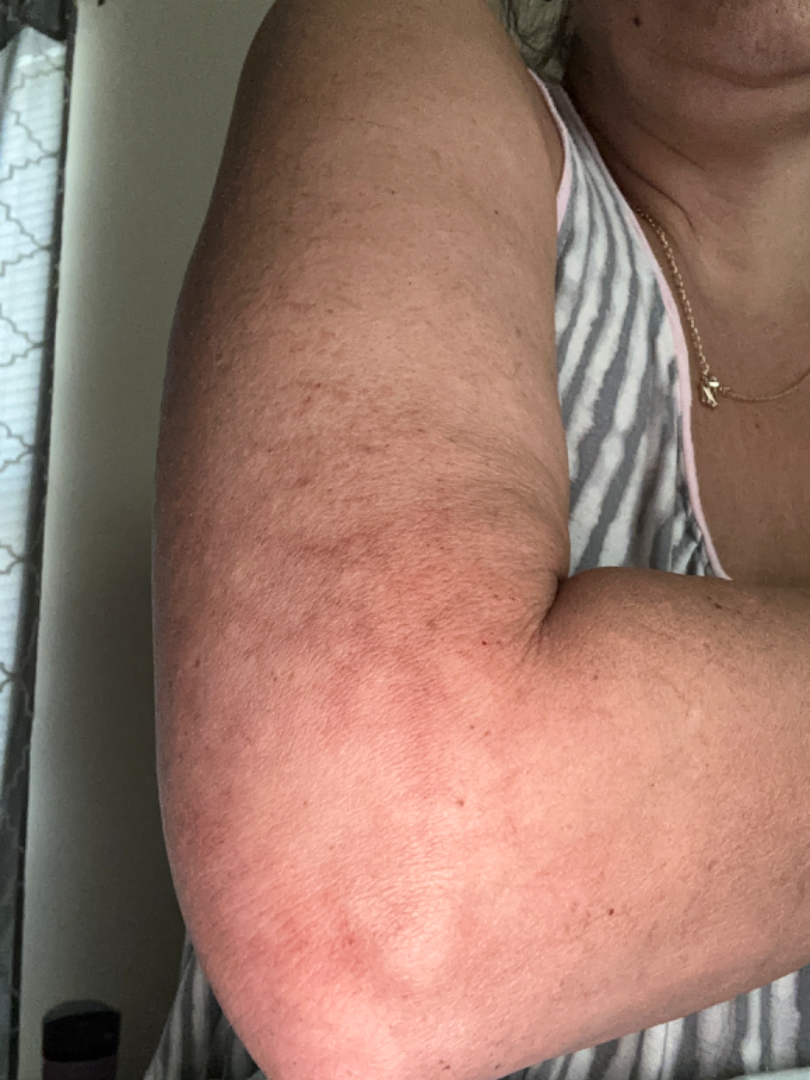{"differential": {"Erythema ab igne": 1.0}}